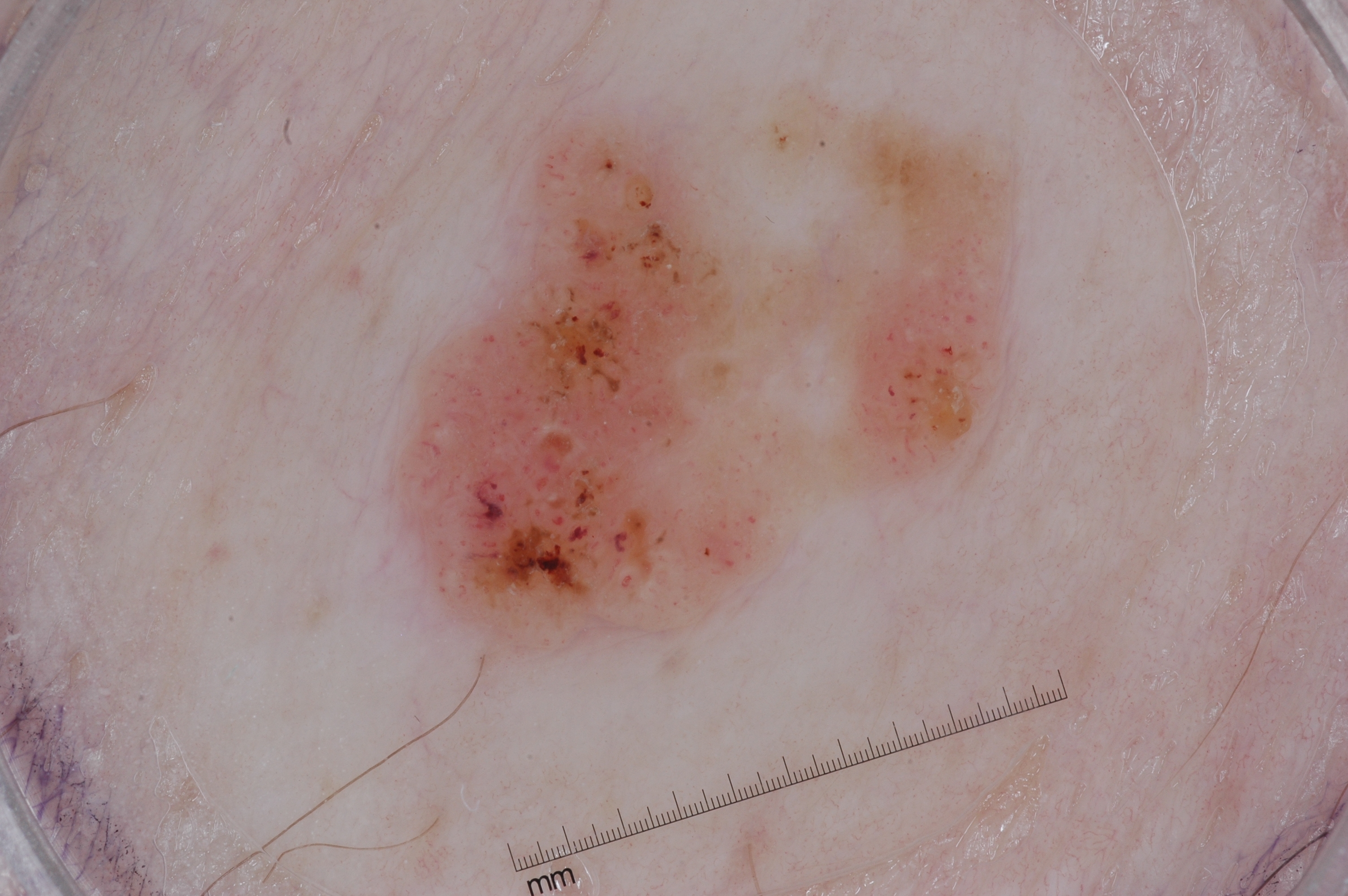Case summary:
* subject · male, aged 78 to 82
* image · dermoscopic image
* features · milia-like cysts
* lesion location · bbox(381, 58, 1029, 675)
* impression · a seborrheic keratosis, a benign skin lesion